A dermoscopic image of a skin lesion.
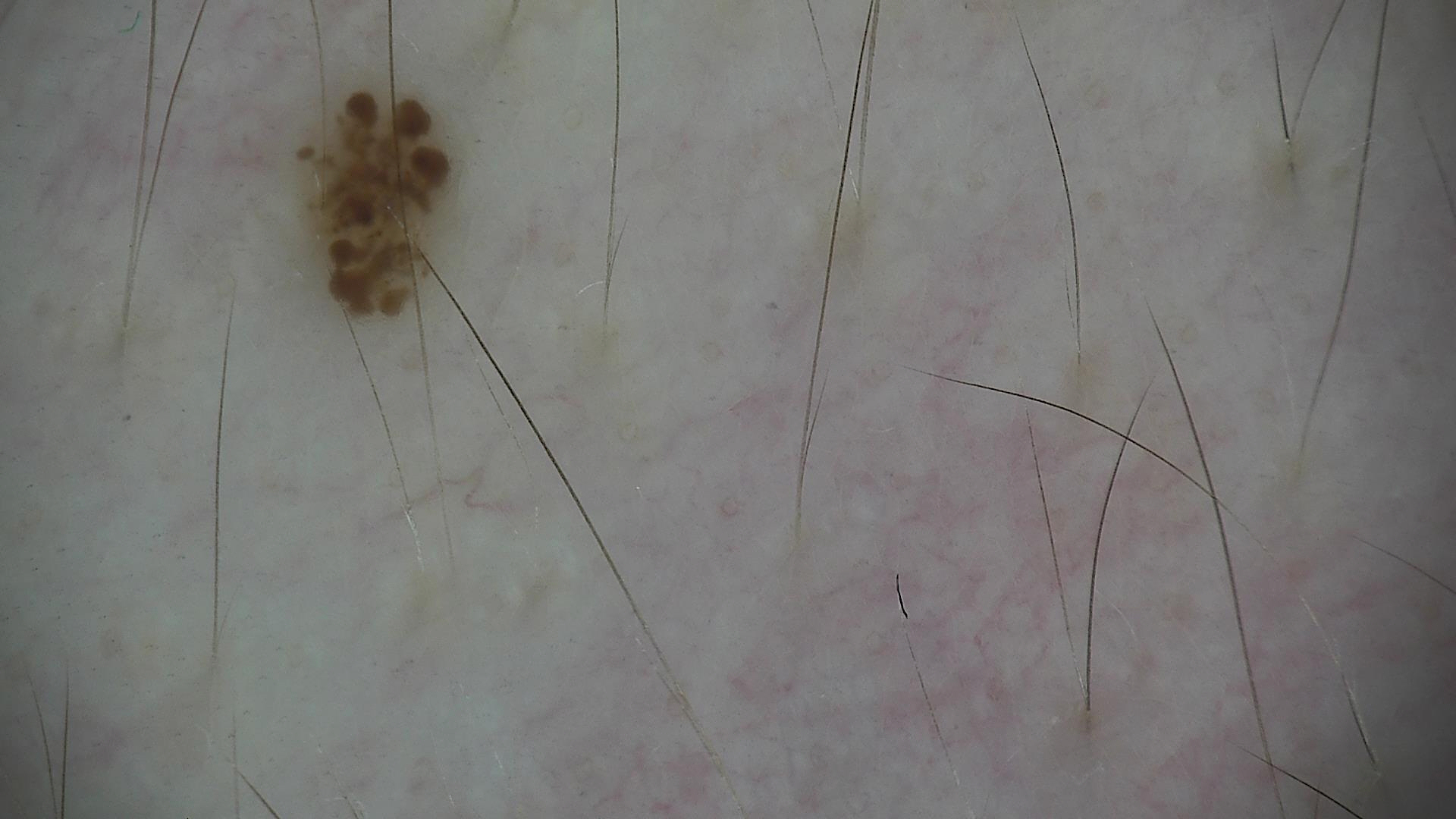{"diagnosis": {"name": "dysplastic junctional nevus", "code": "jd", "malignancy": "benign", "super_class": "melanocytic", "confirmation": "expert consensus"}}